A skin lesion imaged with a dermatoscope; the subject is a female roughly 85 years of age or older.
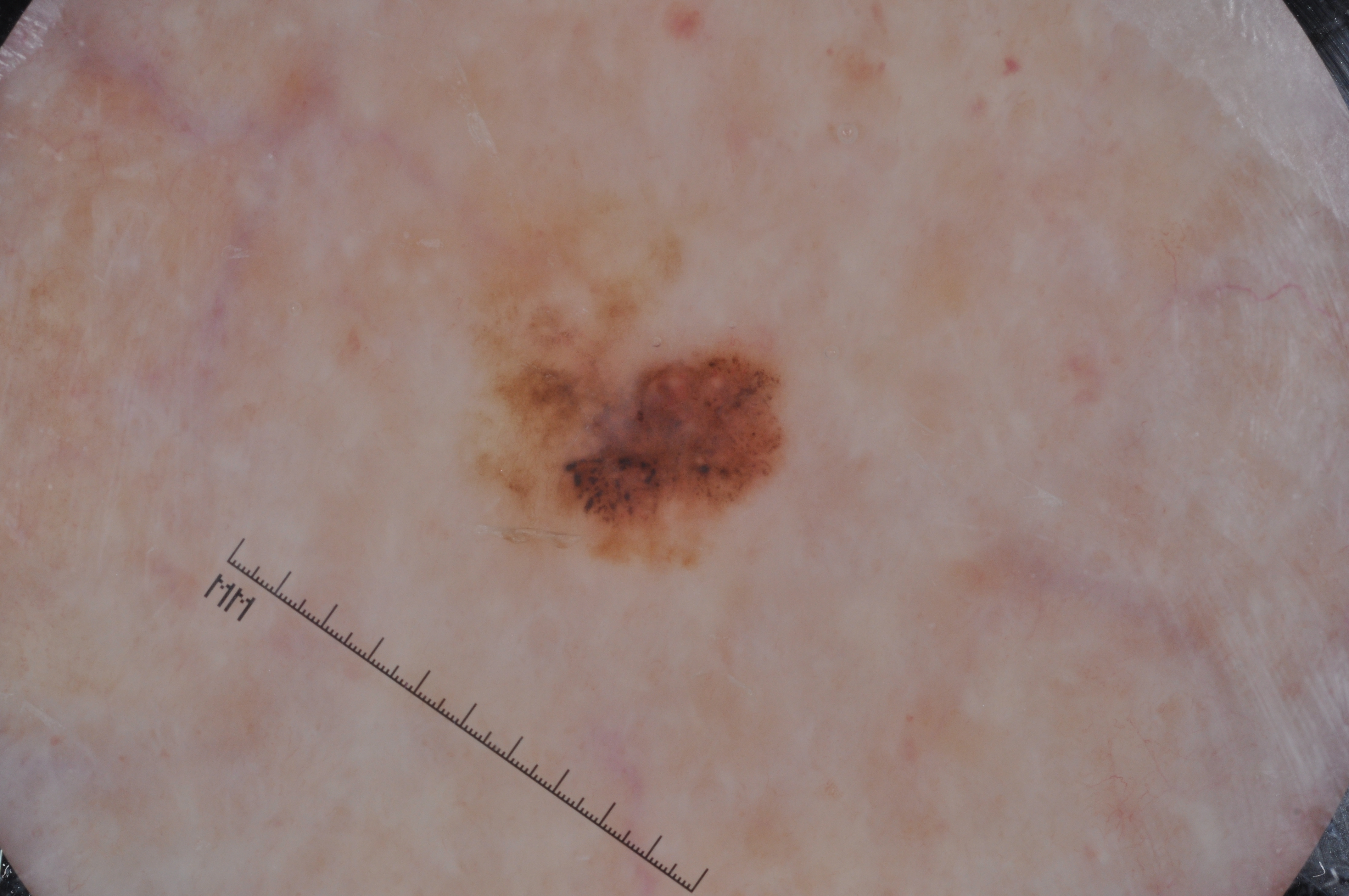Dermoscopic examination shows pigment network. The lesion is bounded by x1=485 y1=301 x2=790 y2=560. The biopsy diagnosis was a melanoma, a skin cancer.